Close-up view · the affected area is the back of the hand and arm · no associated systemic symptoms reported · present for less than one week · the contributor is a female aged 18–29 · the contributor reports the lesion is raised or bumpy · symptoms reported: bothersome appearance, enlargement and itching · the patient described the issue as a rash.
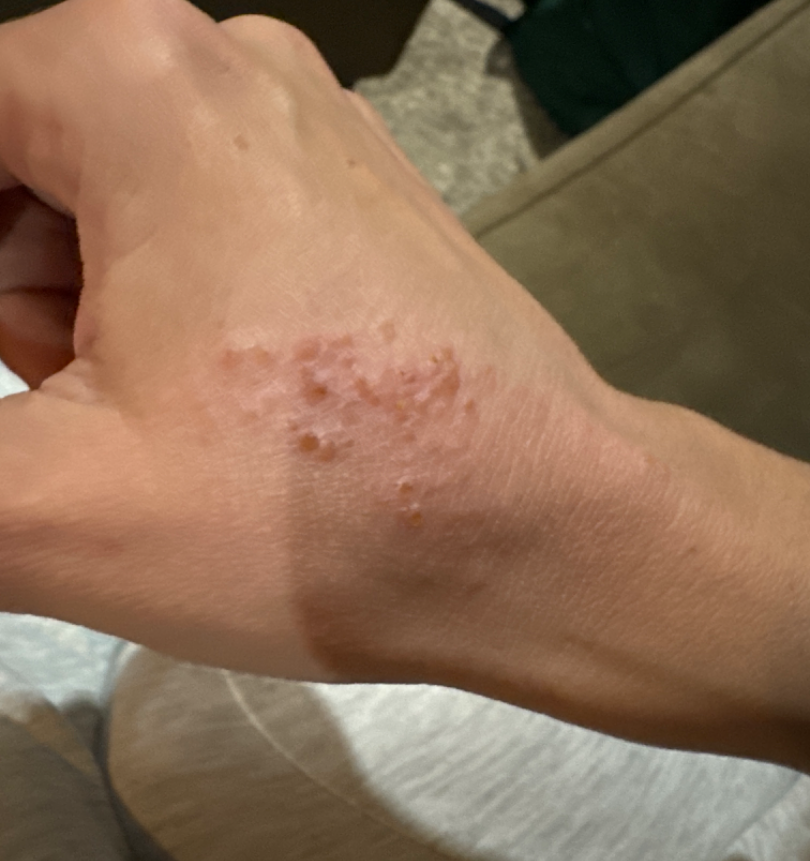Findings:
On teledermatology review: Impetigo (weight 0.33); Herpes Zoster (weight 0.33); Herpes Simplex (weight 0.33).